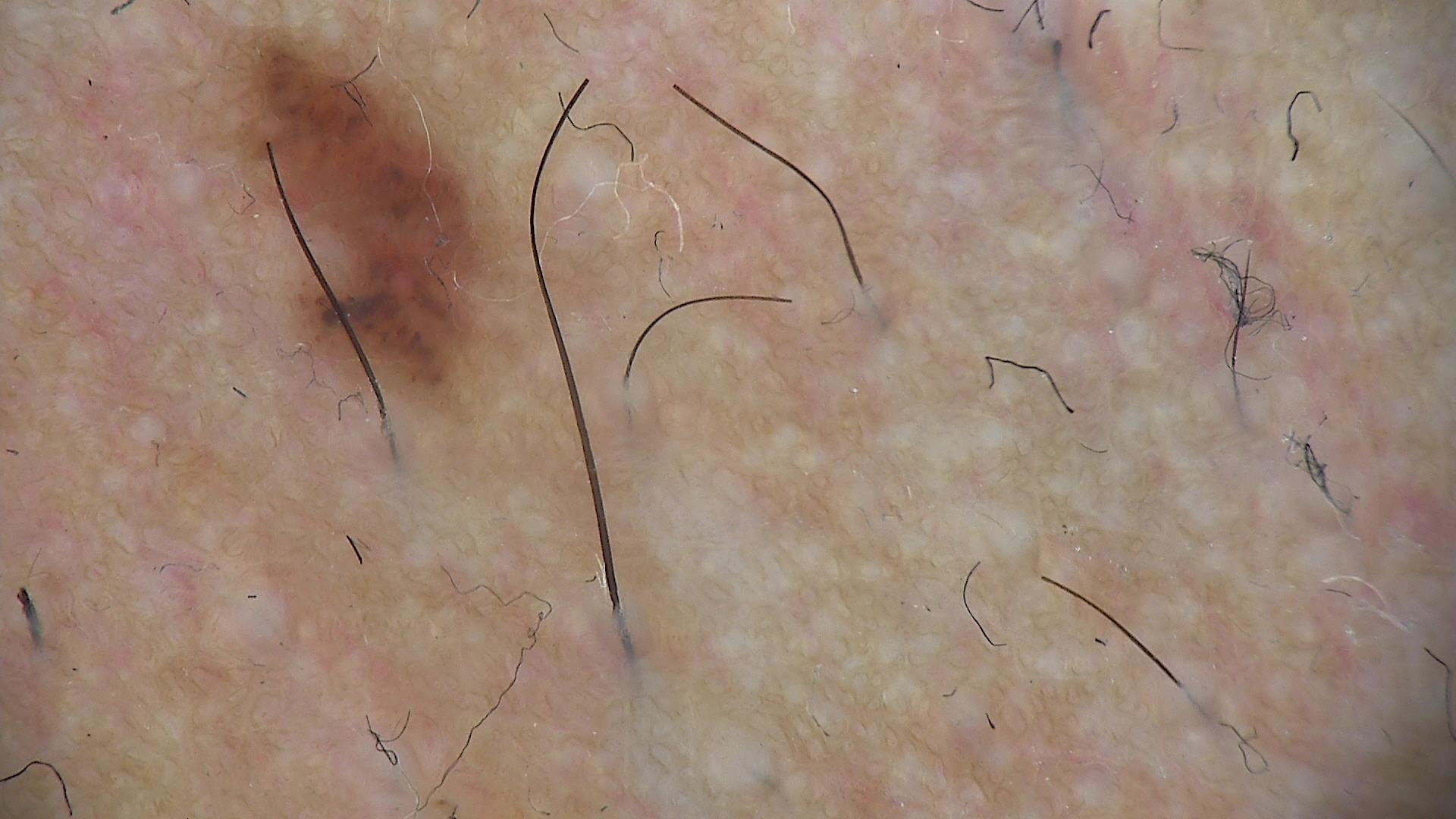class = dysplastic compound nevus (expert consensus).